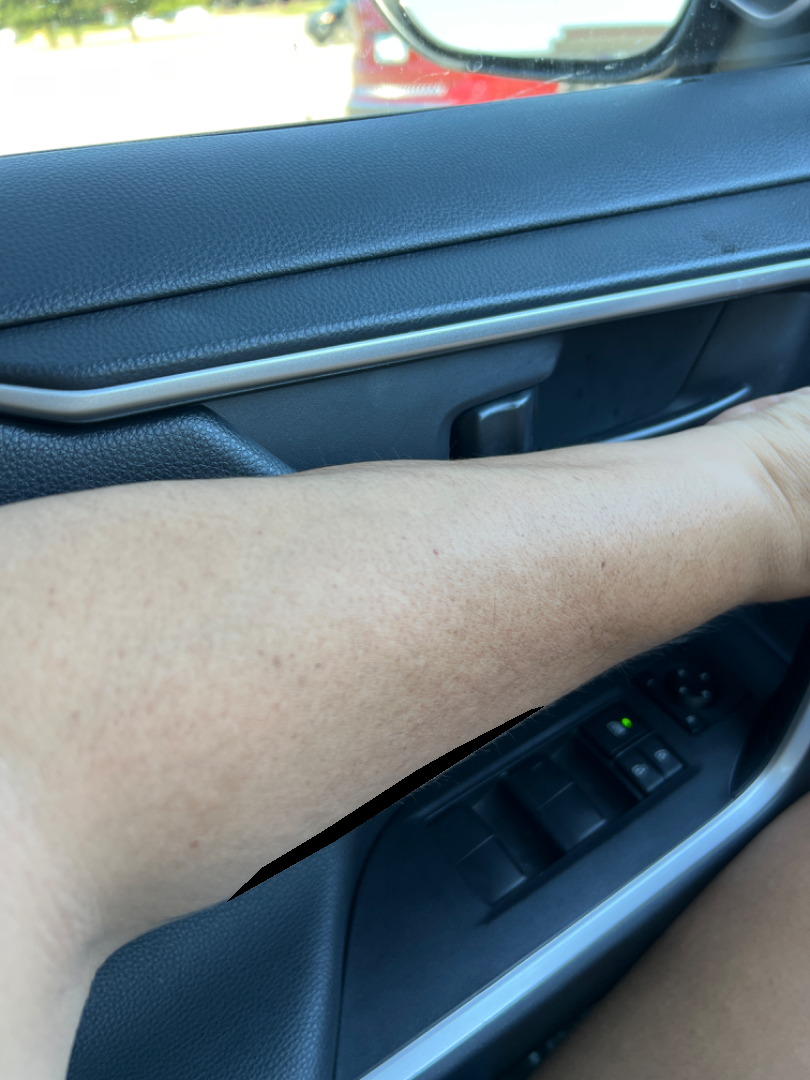assessment=unable to determine | photo taken=at a distance | described texture=rough or flaky and flat | patient describes the issue as=a rash | onset=about one day | reported symptoms=none reported | location=arm and leg.